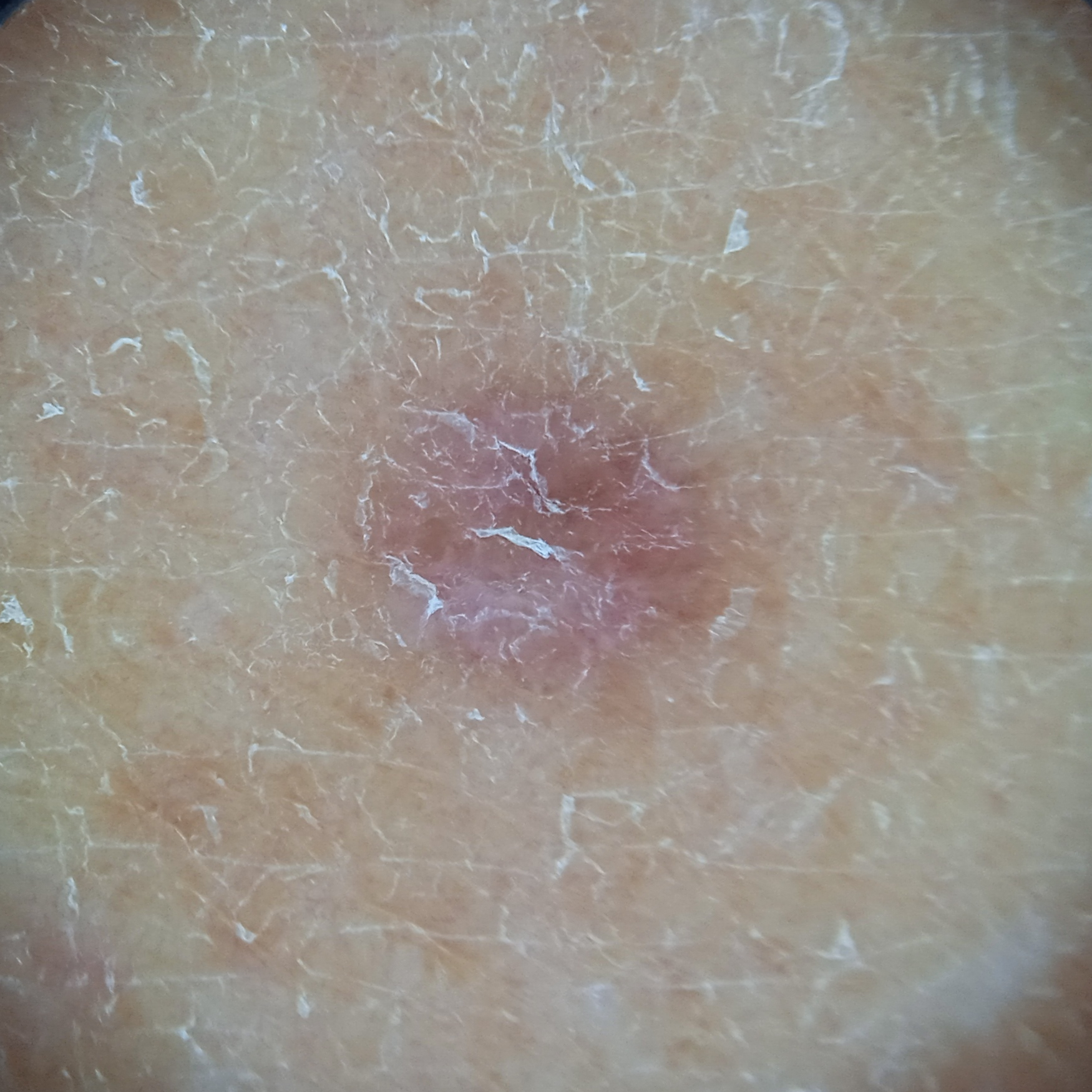{"patient": {"age": 58, "sex": "female"}, "risk_factors": {"positive": ["a personal history of cancer", "a family history of skin cancer", "a personal history of skin cancer"]}, "image": "dermoscopic image", "mole_burden": "a moderate number of melanocytic nevi", "lesion_size": {"diameter_mm": 5.2}, "diagnosis": {"name": "dermatofibroma", "malignancy": "benign"}}